The patient is a female aged 53 to 57; a dermoscopic close-up of a skin lesion: 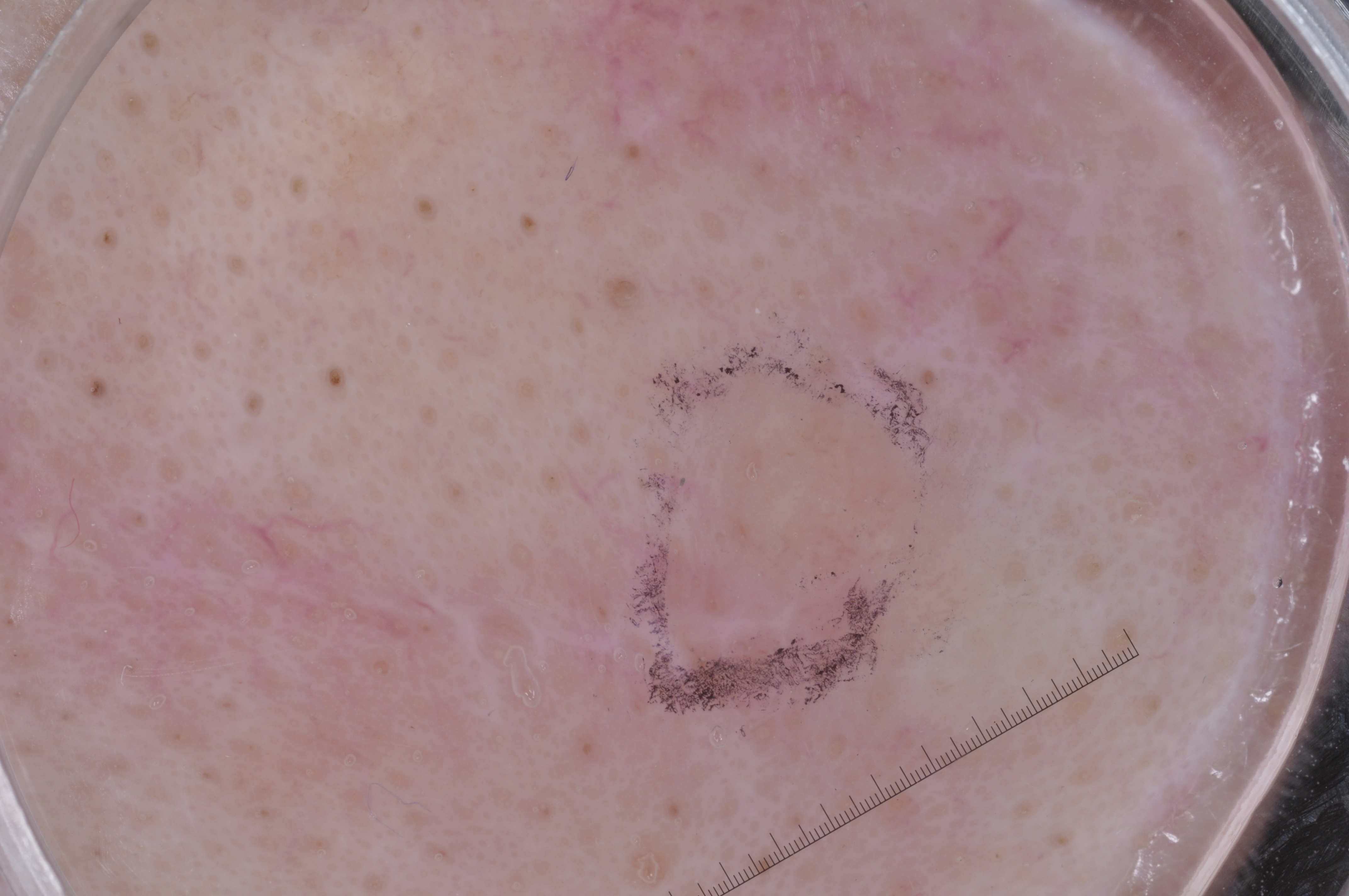Q: Which dermoscopic features are absent?
A: milia-like cysts, negative network, pigment network, and streaks
Q: How large is the lesion within the image?
A: ~5% of the field
Q: Where is the lesion located?
A: bbox(656, 369, 923, 694)
Q: What is the diagnosis?
A: a melanoma, a malignant lesion